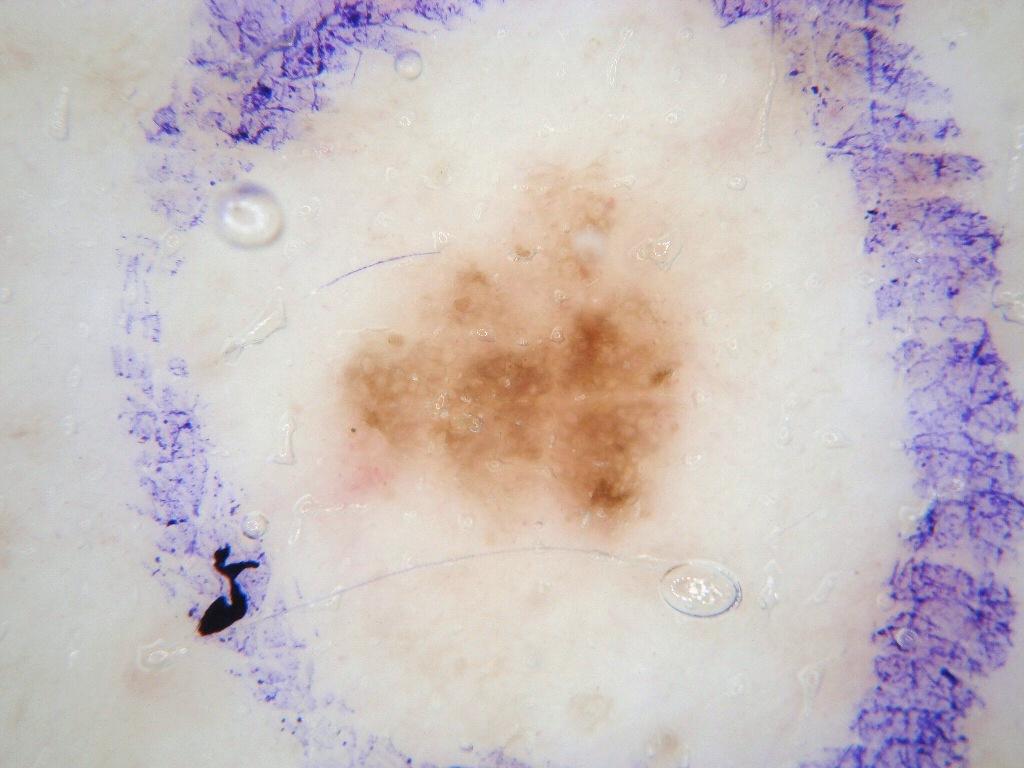Summary: A dermoscopy image of a single skin lesion. A male subject in their 50s. In (x1, y1, x2, y2) order, the lesion's extent is 327/162/700/553. The lesion covers approximately 12% of the dermoscopic field. Dermoscopic examination shows globules and pigment network. Conclusion: Expert review diagnosed this as a melanocytic nevus, a benign skin lesion.